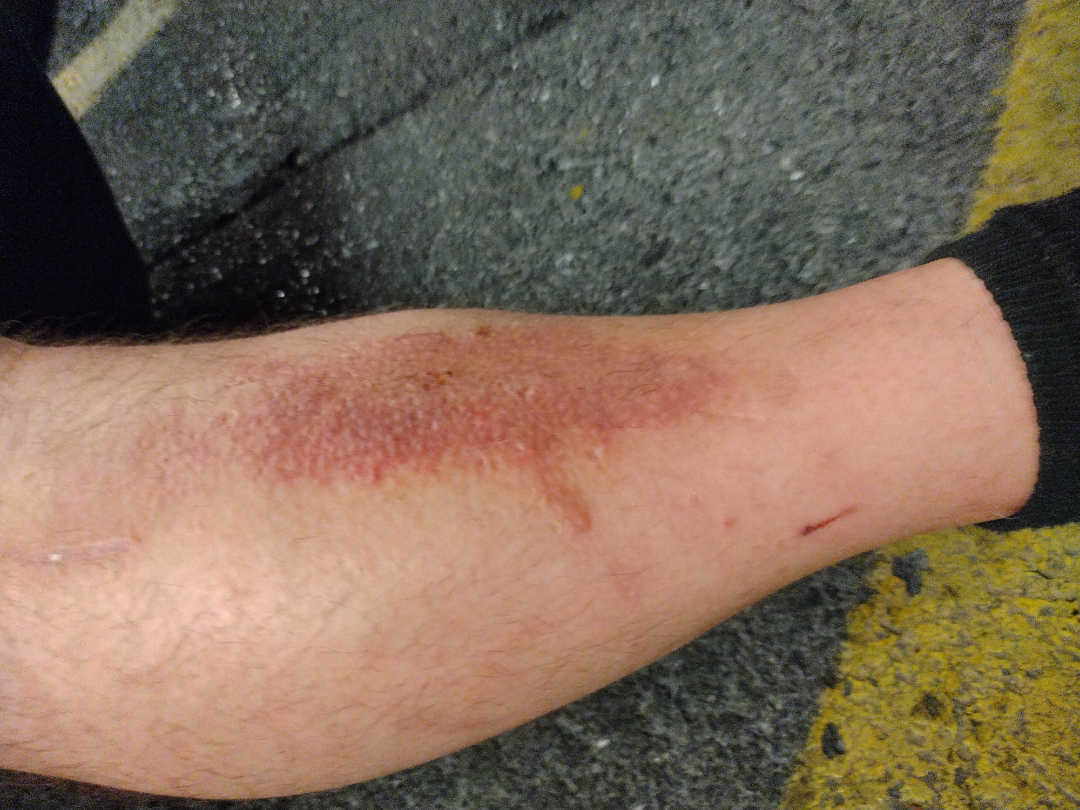| field | value |
|---|---|
| impression | Allergic Contact Dermatitis (54%); Eczema (23%); Amyloidosis of skin (23%) |